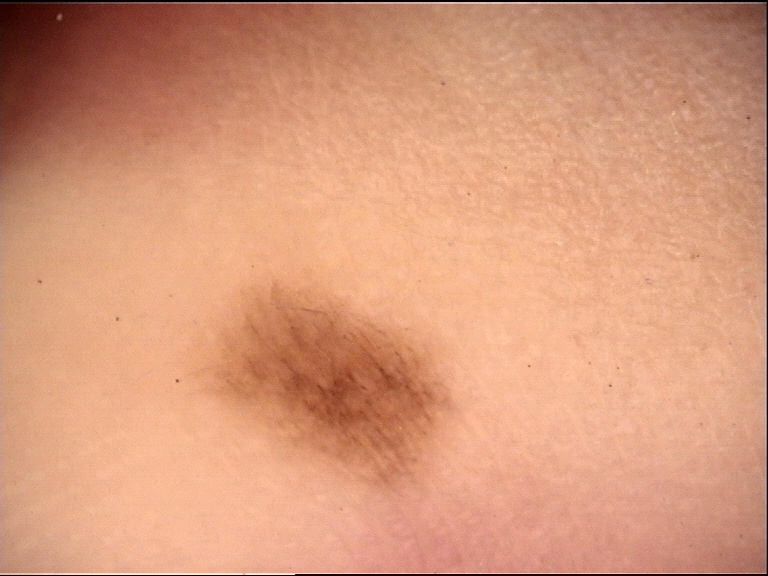label — acral dysplastic junctional nevus (expert consensus).